A dermatoscopic image of a skin lesion: 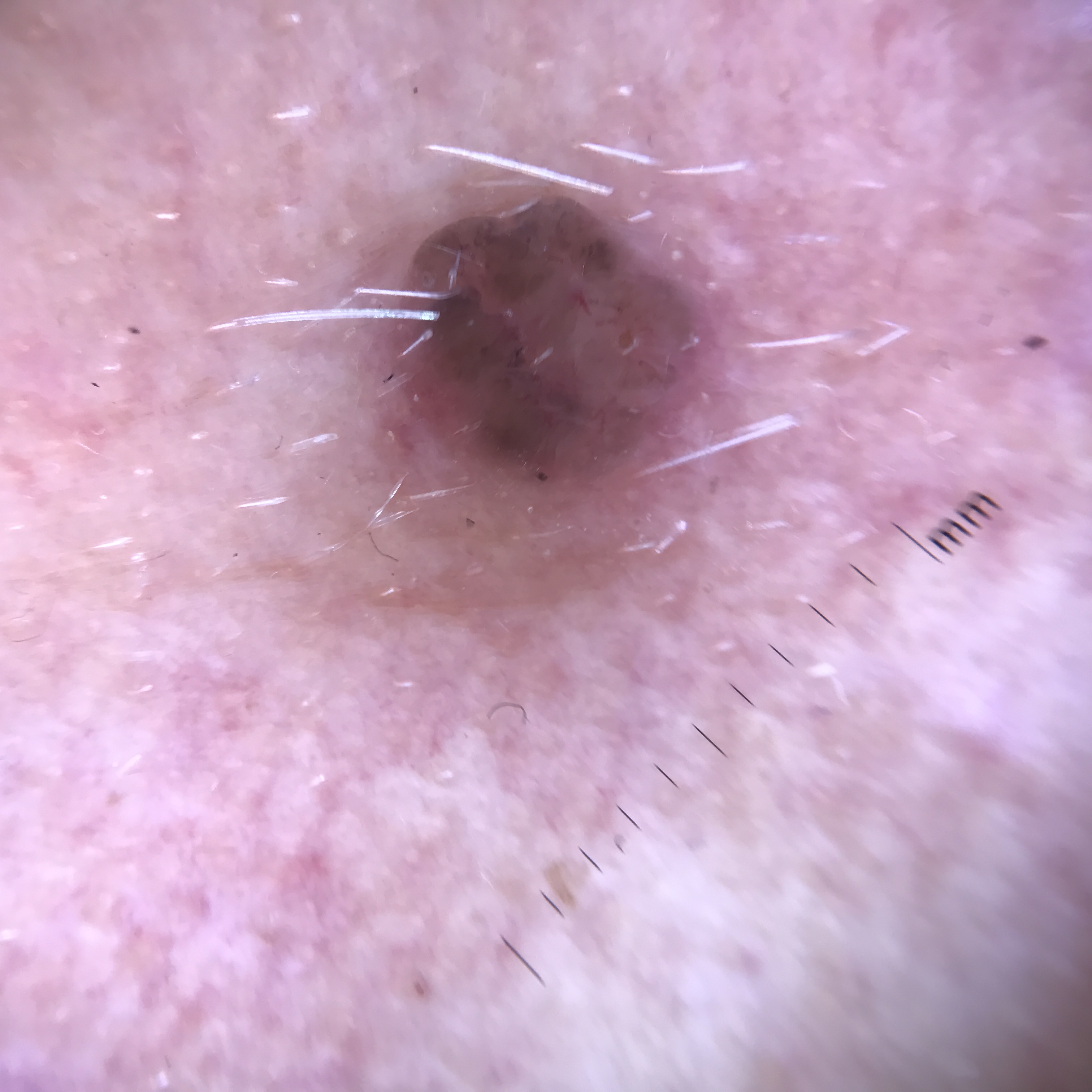Biopsy-confirmed as a basal cell carcinoma.